Female contributor, age 40–49 · the photograph is a close-up of the affected area · the patient reports bothersome appearance and enlargement · the lesion involves the head or neck · the lesion is described as rough or flaky and raised or bumpy · the condition has been present for one to three months — 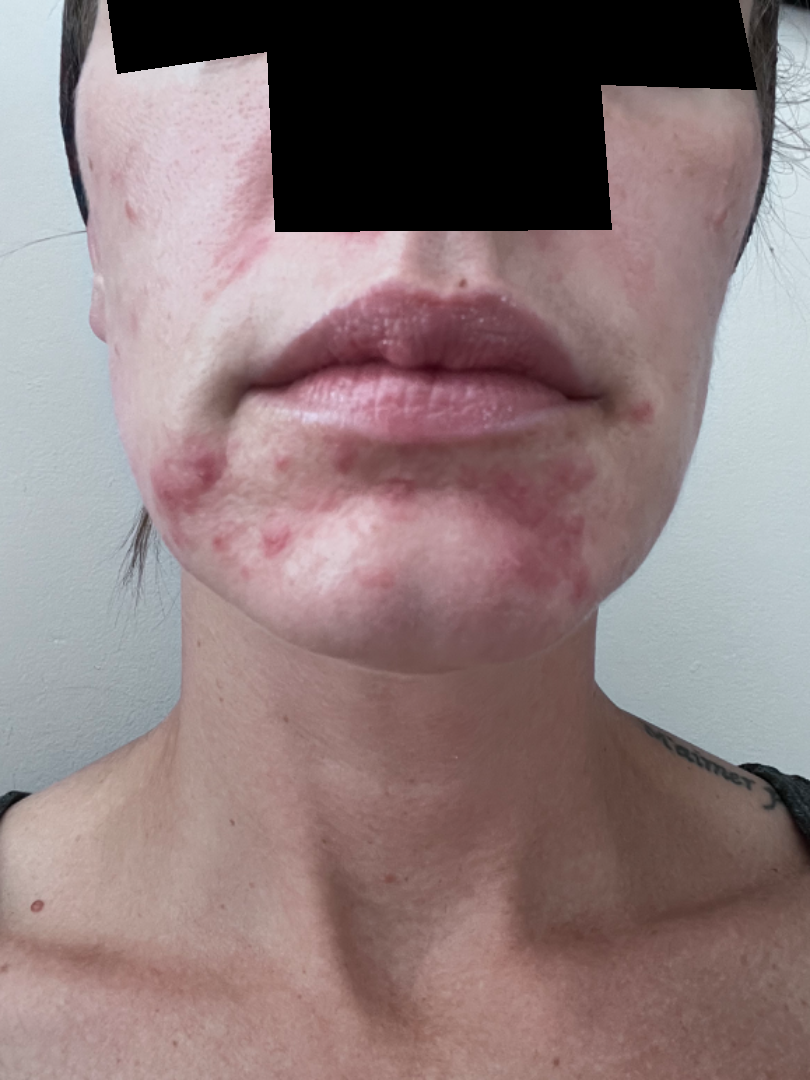assessment=the differential is split between Rosacea and Perioral Dermatitis.